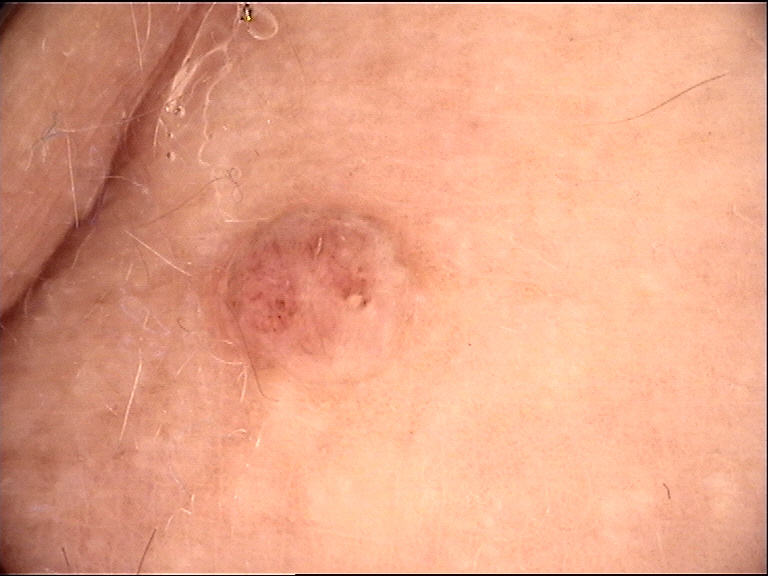The diagnostic label was a dermal nevus.